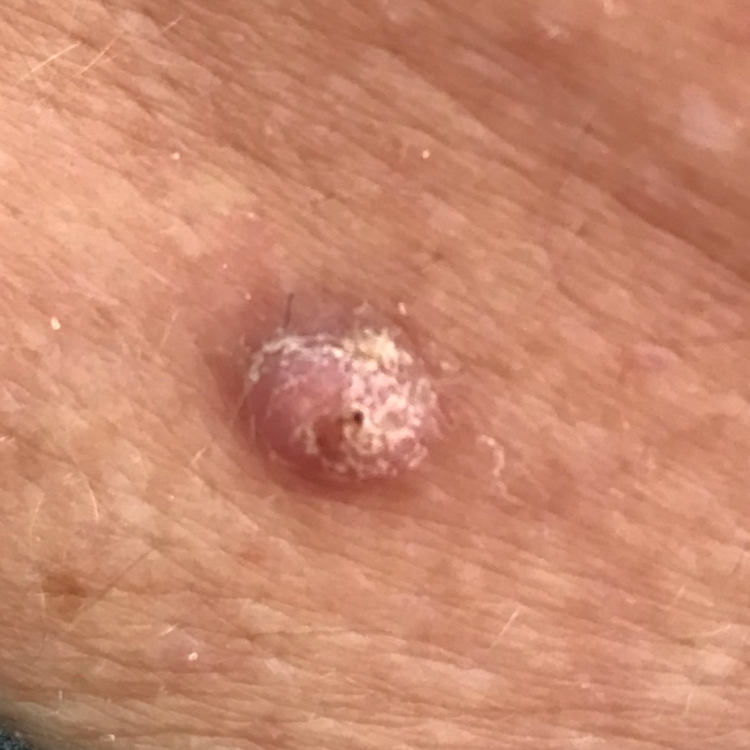The patient was assessed as Fitzpatrick II. A male patient aged 69. A clinical photo of a skin lesion taken with a smartphone. The lesion was found on the back. The lesion is roughly 7 by 7 mm. Per patient report, the lesion is elevated. Histopathology confirmed a squamous cell carcinoma.